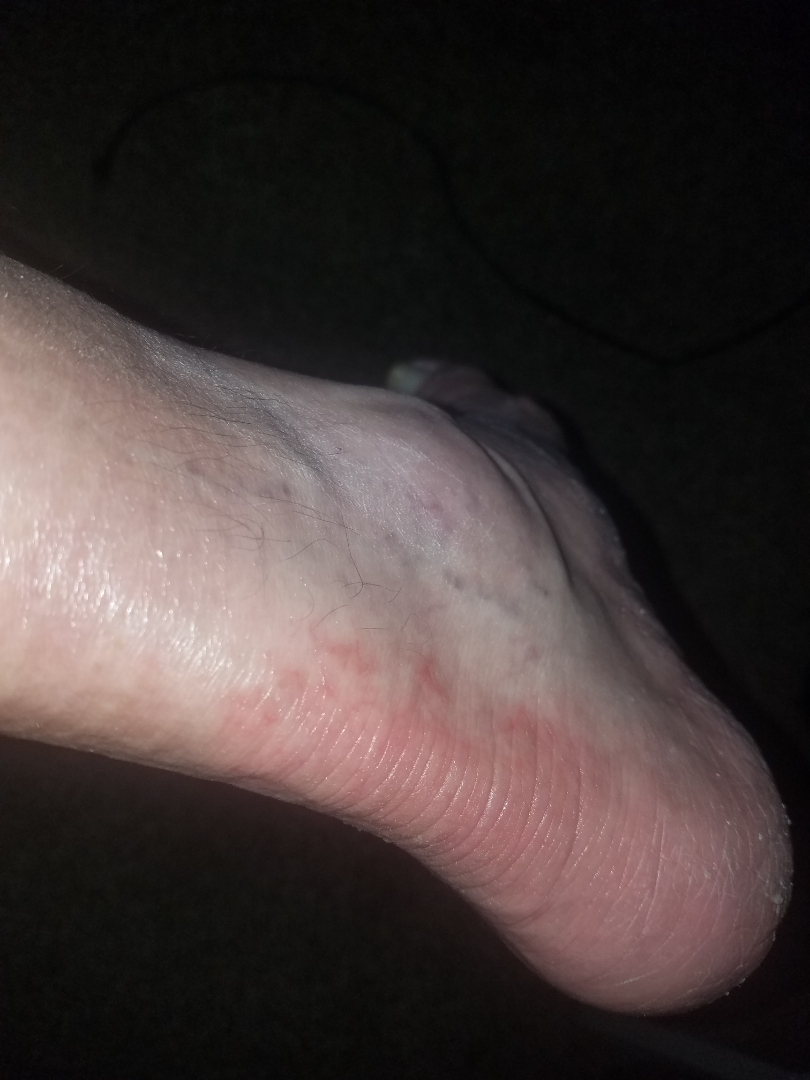photo taken = at an angle
patient = male, age 50–59
differential = the favored diagnosis is Tinea; less probable is Eczema; a remote consideration is Psoriasis